Dermoscopy of a skin lesion — 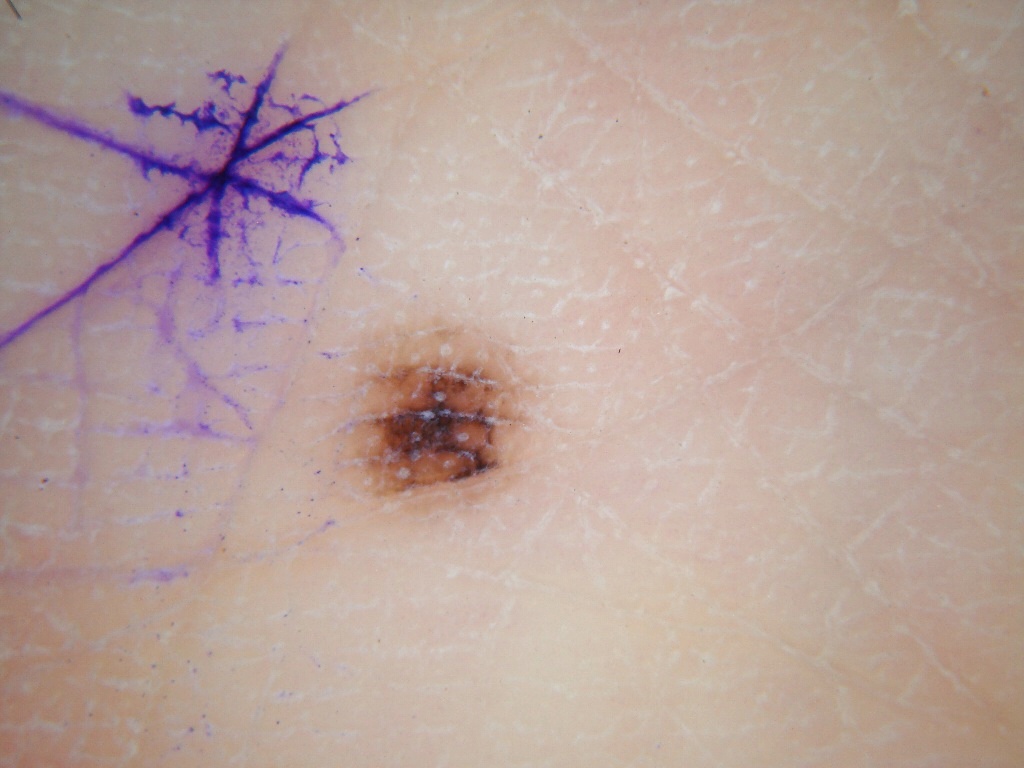Image and clinical context: Dermoscopic review identifies no pigment network, globules, milia-like cysts, negative network, or streaks. With coordinates (x1, y1, x2, y2), lesion location: bbox(333, 329, 521, 512). Impression: The clinical diagnosis was a melanocytic nevus, a benign lesion.